The contributor notes the lesion is flat. The contributor notes the condition has been present for less than one week. The patient described the issue as a rash. The lesion involves the back of the torso, top or side of the foot, front of the torso, head or neck, leg and back of the hand. This image was taken at a distance.
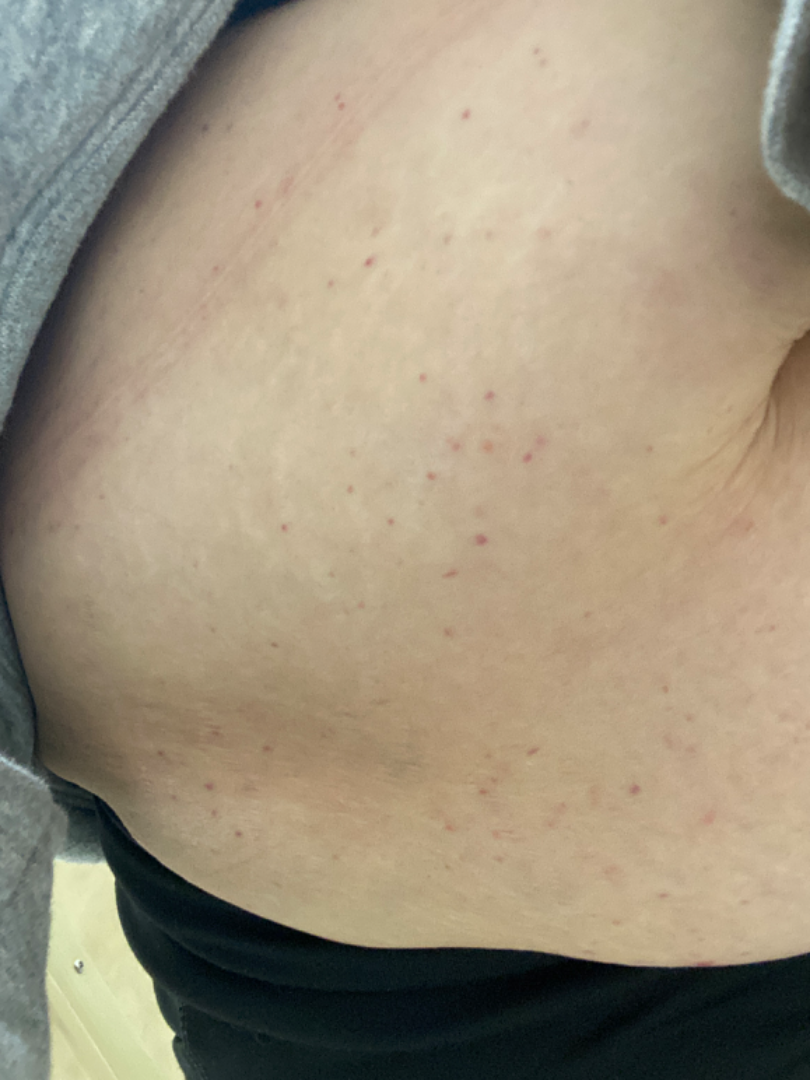| feature | finding |
|---|---|
| differential | the leading impression is Folliculitis; an alternative is Acne |